This image was taken at an angle · the arm and head or neck are involved.
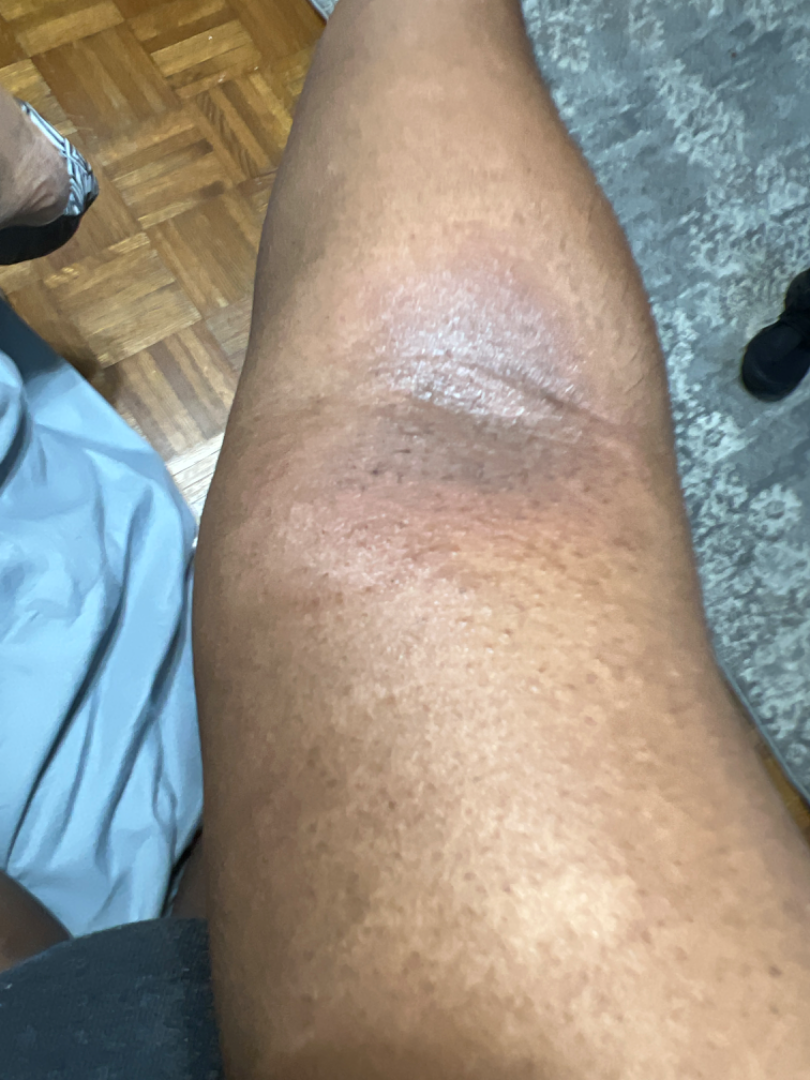  texture: flat
  skin_tone:
    fitzpatrick: V
  patient_category: a rash
  symptoms:
    - darkening
    - itching
  differential:
    leading:
      - Eczema